A clinical photograph of a skin lesion; the chart records prior skin cancer (patient or family), prior malignancy (patient or family), pesticide exposure, no tobacco use, and no alcohol use; skin type II; a female patient aged 70: 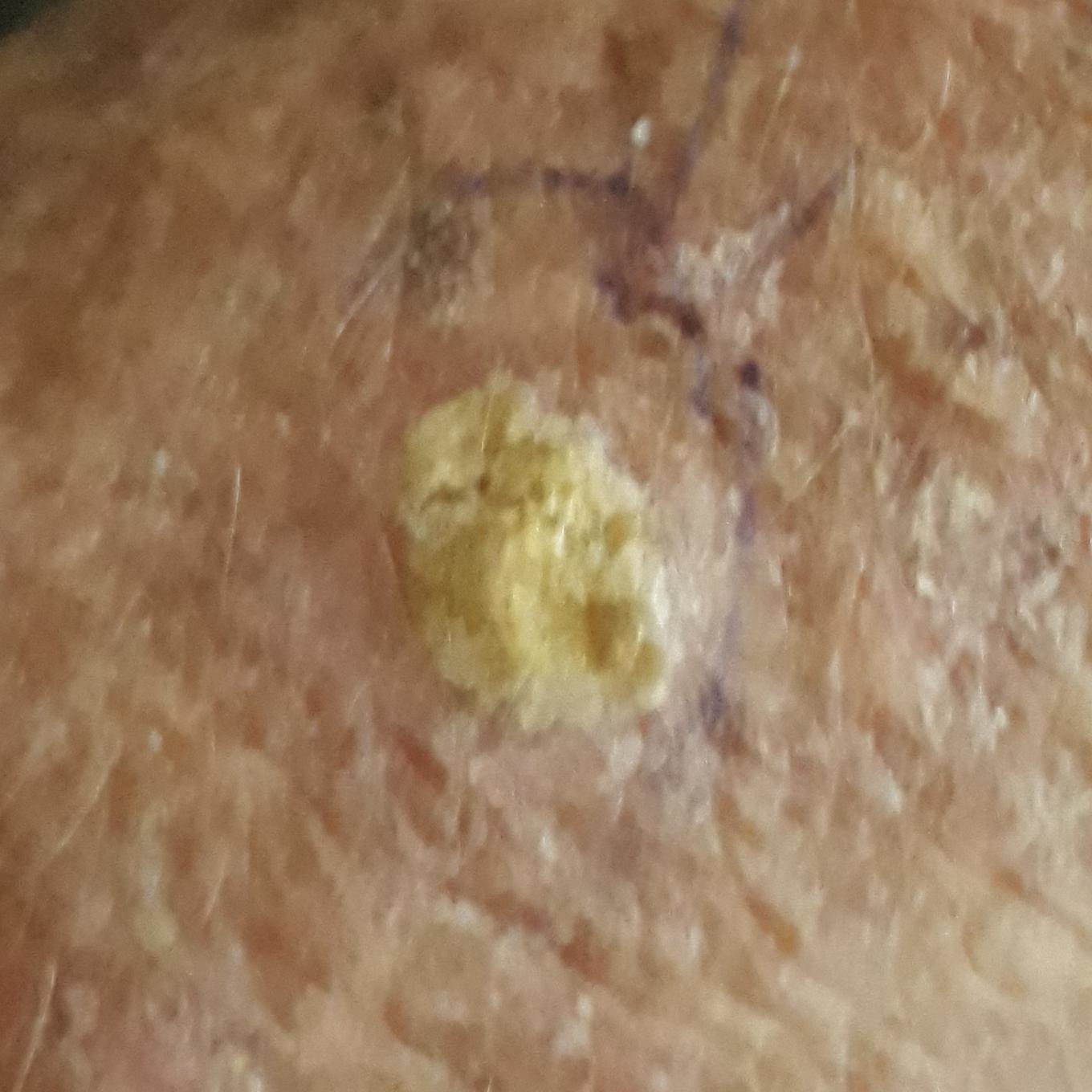| key | value |
|---|---|
| body site | a forearm |
| diameter | 10x9 mm |
| reported symptoms | growth, elevation |
| diagnosis | actinic keratosis (biopsy-proven) |